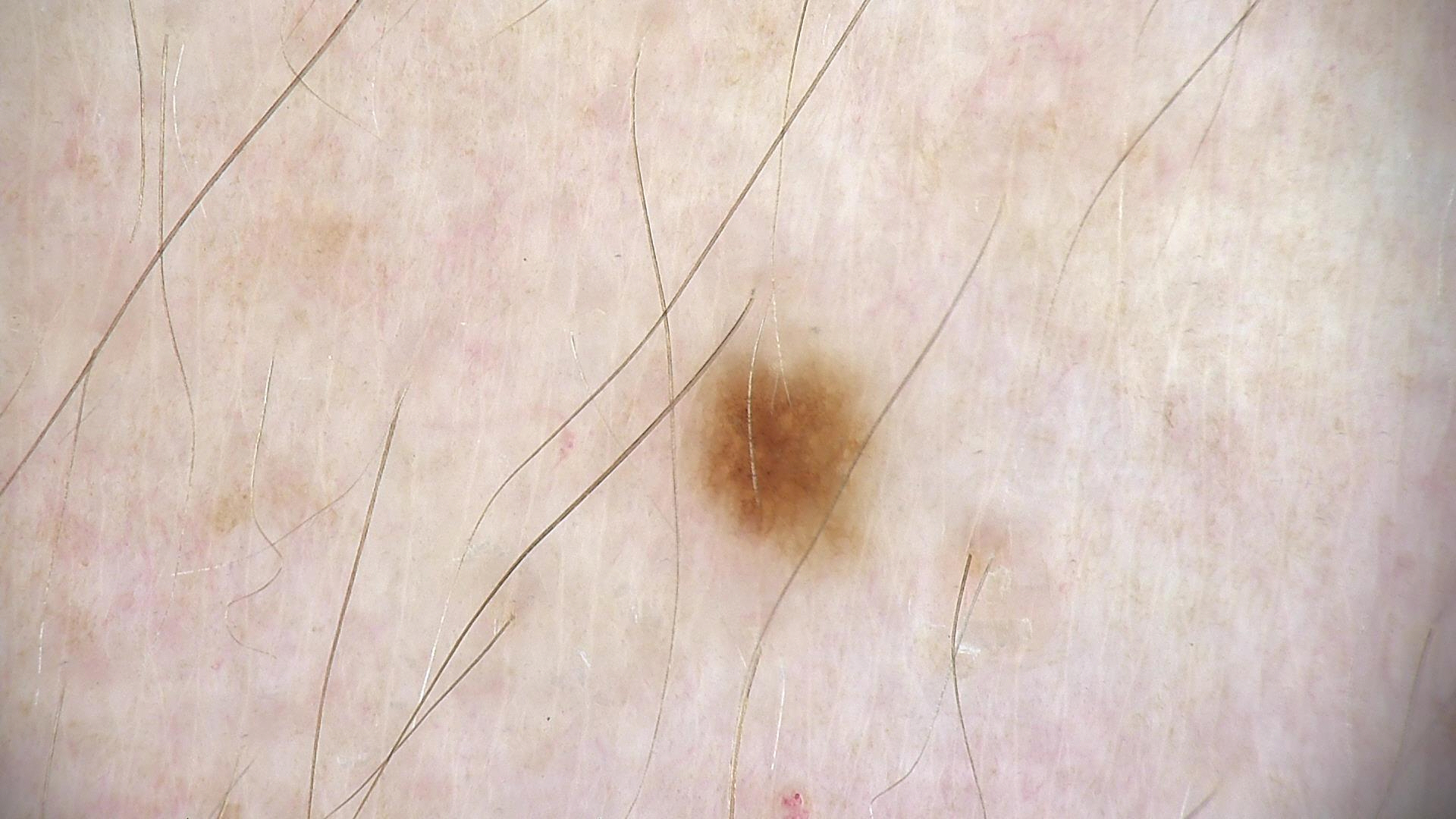Conclusion:
Diagnosed as a dysplastic junctional nevus.